A dermoscopic image of a skin lesion: 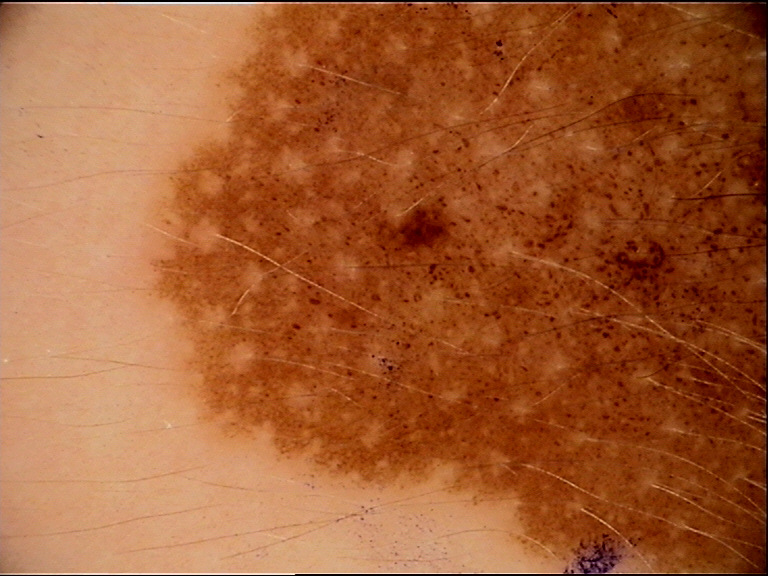This is a banal lesion. Classified as a congenital junctional nevus.